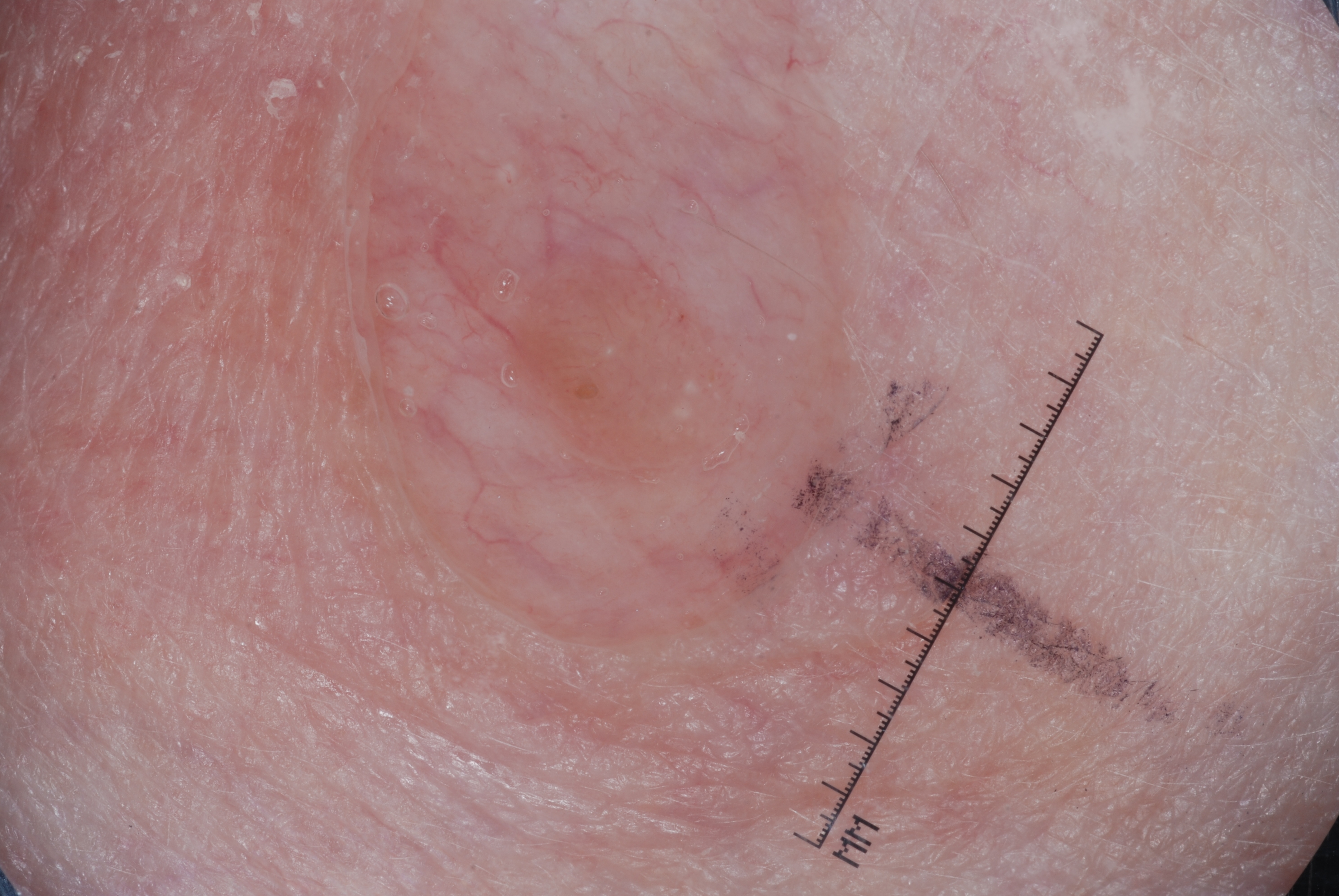* patient · female, roughly 75 years of age
* imaging · dermoscopy
* features · milia-like cysts; absent: streaks, pigment network, and negative network
* lesion location · 494 259 758 480
* lesion extent · small
* diagnosis · a seborrheic keratosis